A male patient in their 40s · recorded as Fitzpatrick phototype III · per the chart, melanoma in a first-degree relative.
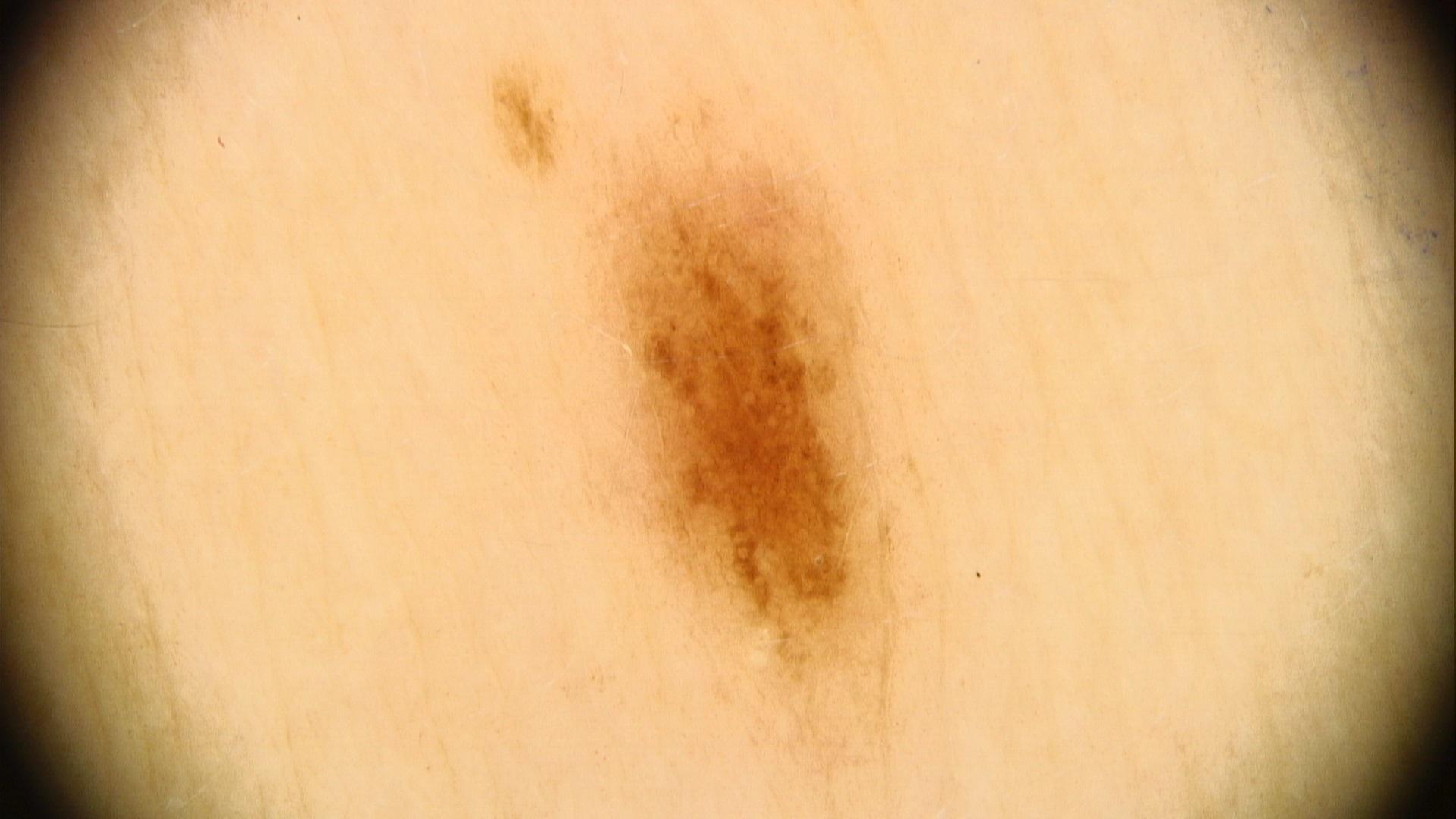Located on the trunk (the anterior trunk).
Clinically diagnosed as a benign lesion — a nevus.